A female subject aged approximately 65; a dermoscopic image of a skin lesion: 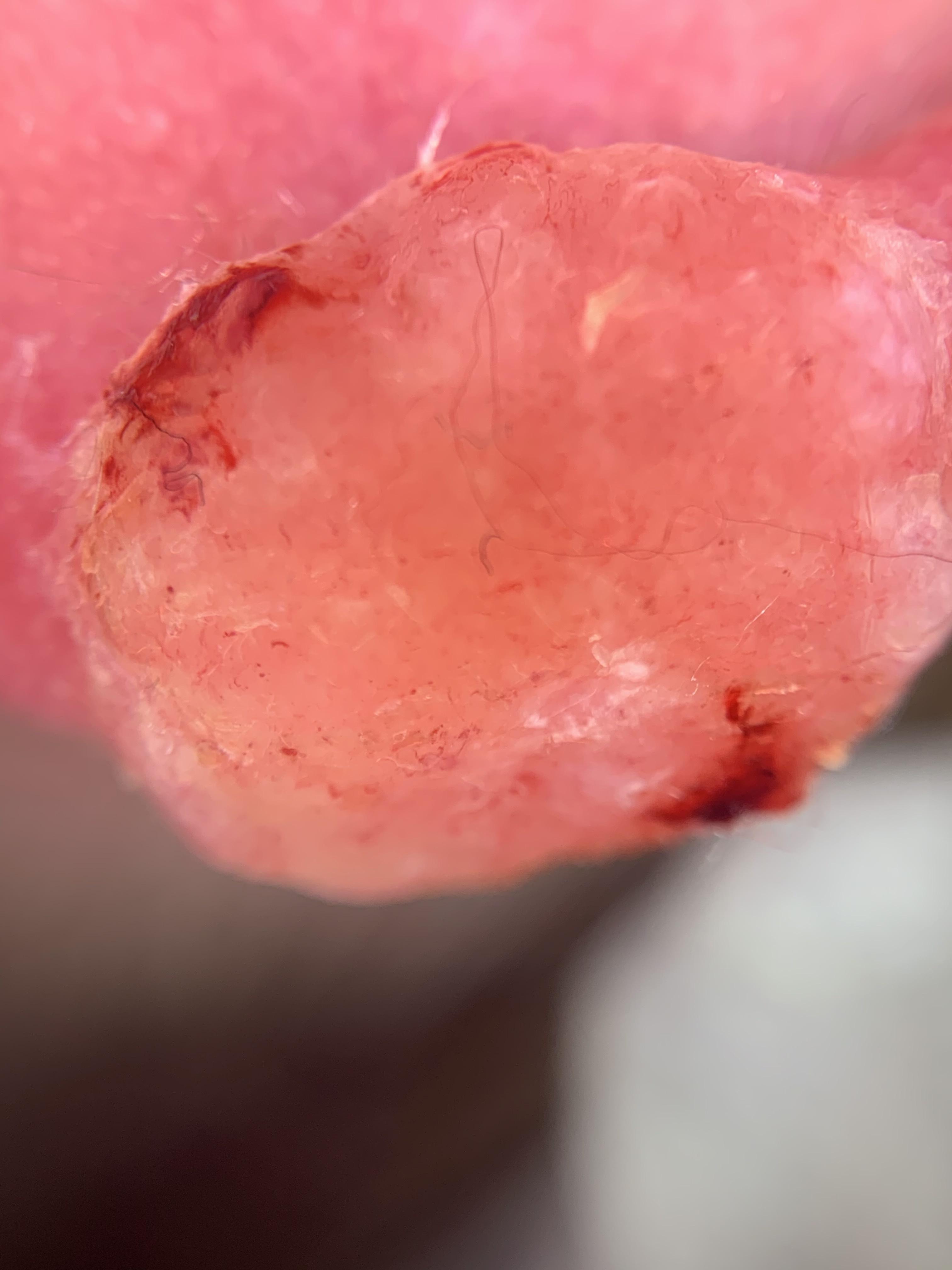The lesion is on the head or neck. The biopsy diagnosis was a squamous cell carcinoma.